A male subject aged 33 to 37.
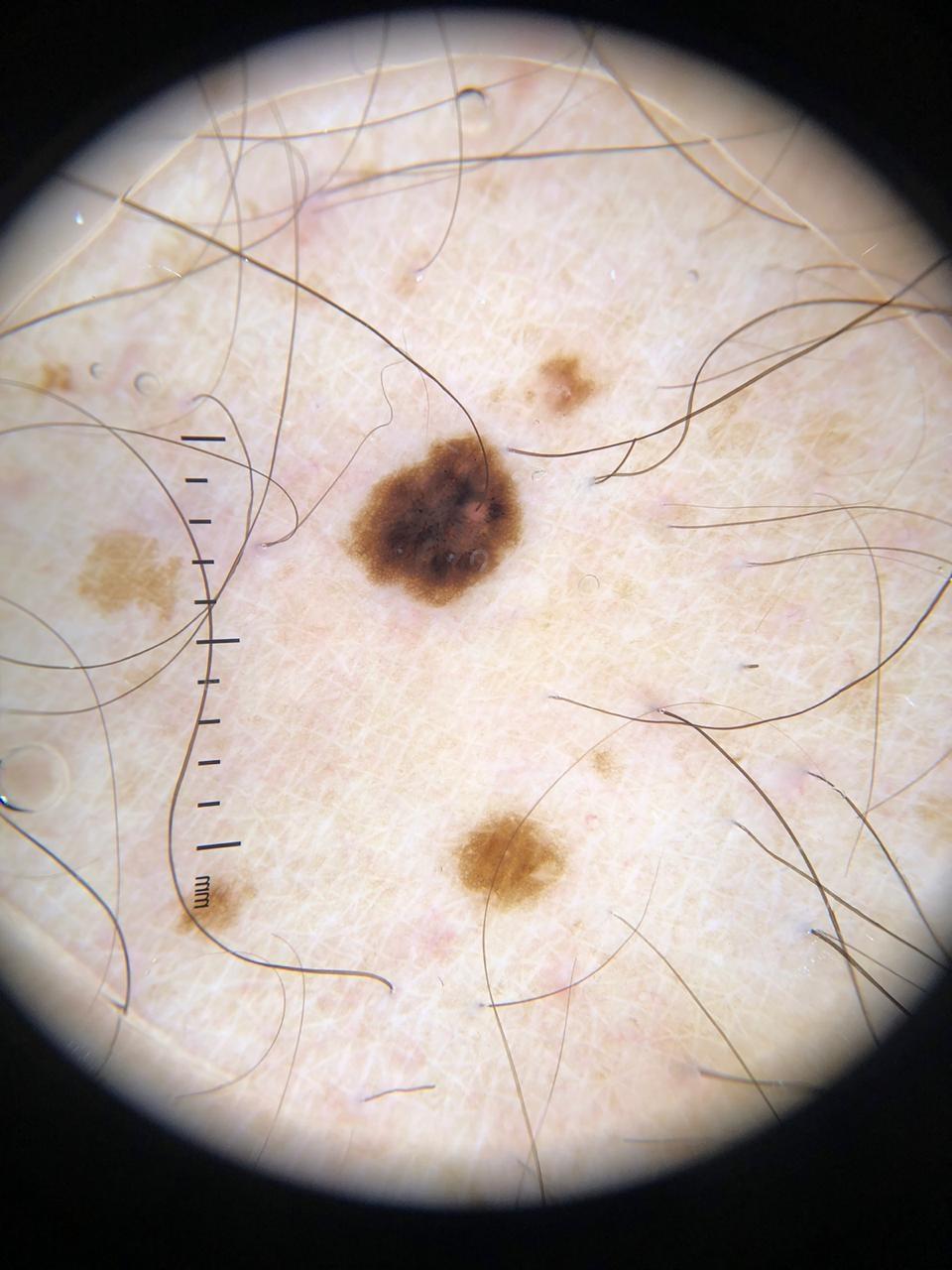Q: What is this lesion?
A: Nevus (biopsy-proven)